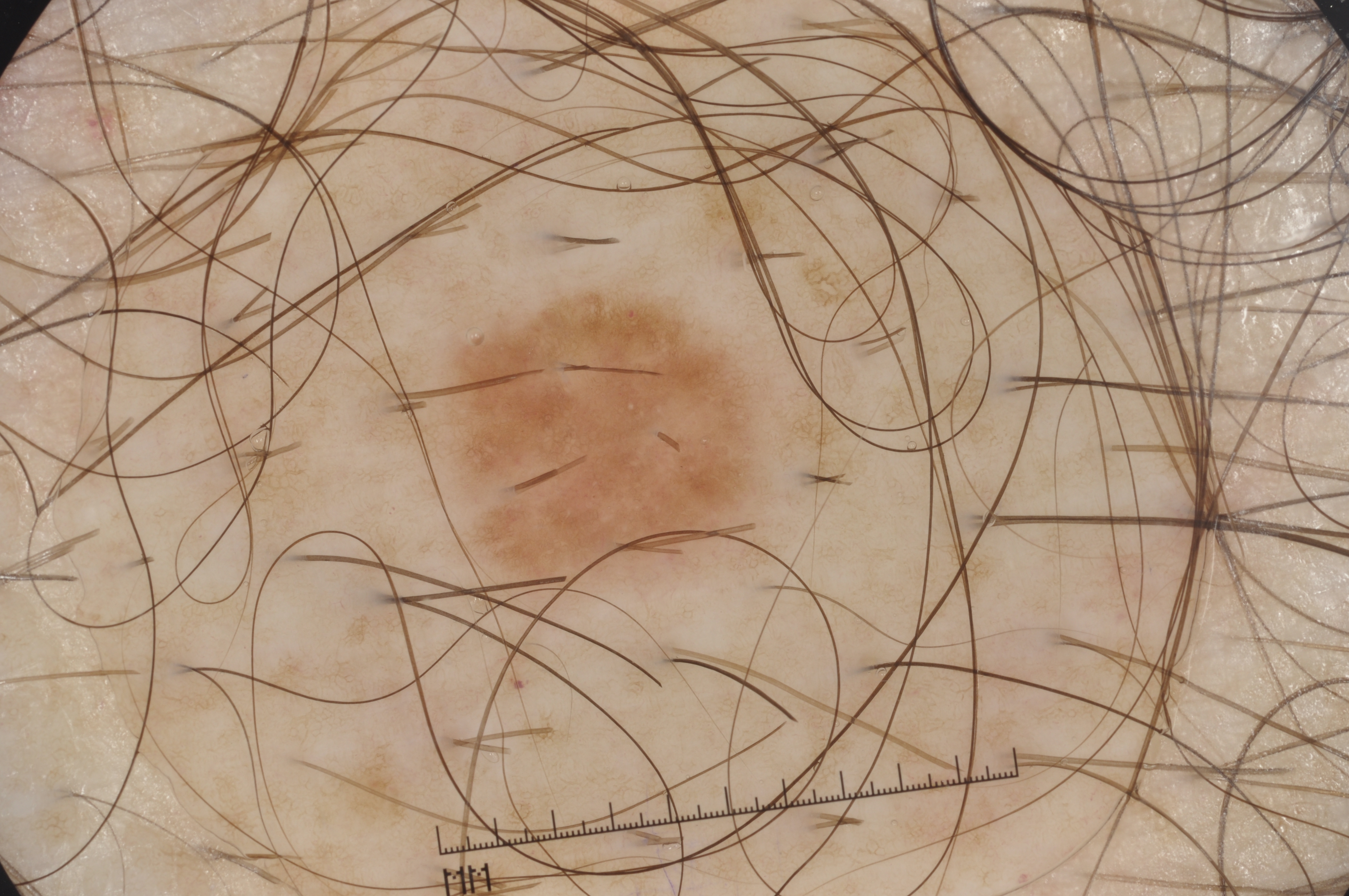Findings:
The subject is a male aged around 55. A dermoscopy image of a single skin lesion. As (left, top, right, bottom), the lesion occupies the region bbox=[453, 294, 748, 588]. The lesion covers approximately 6% of the dermoscopic field. On dermoscopy, the lesion shows pigment network and milia-like cysts; no streaks or negative network.
Assessment:
Consistent with a melanocytic nevus, a benign skin lesion.